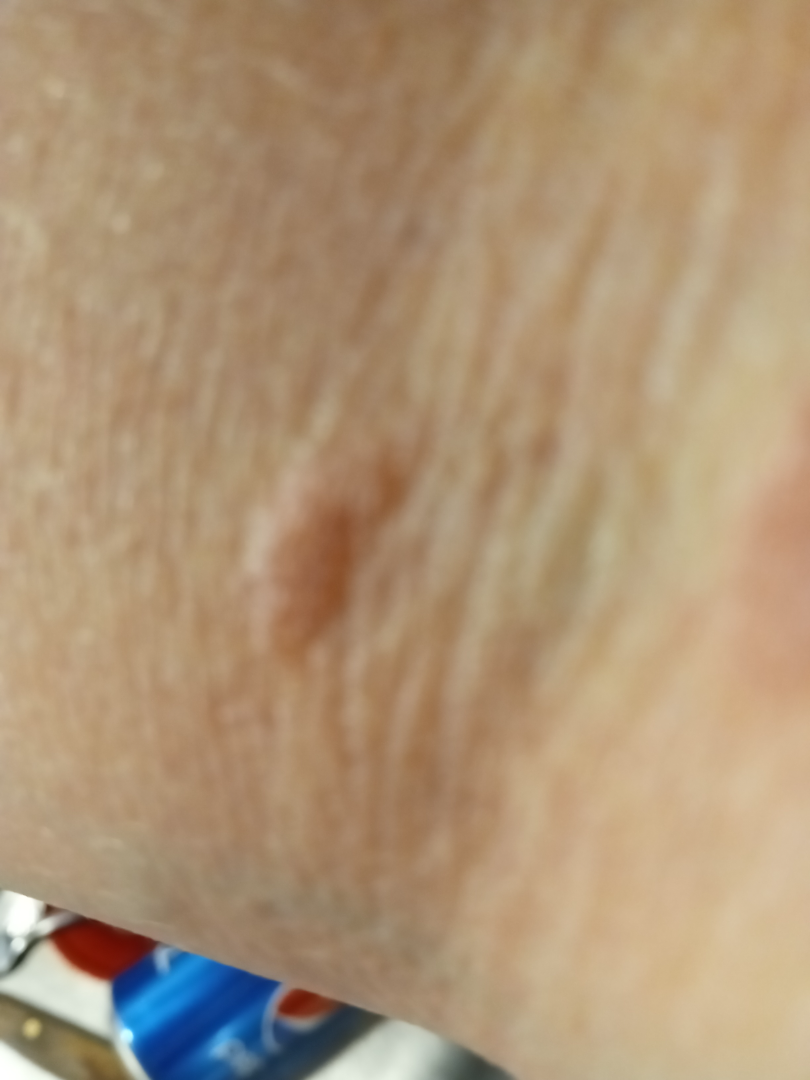Q: Could the case be diagnosed?
A: could not be assessed
Q: Image view?
A: close-up